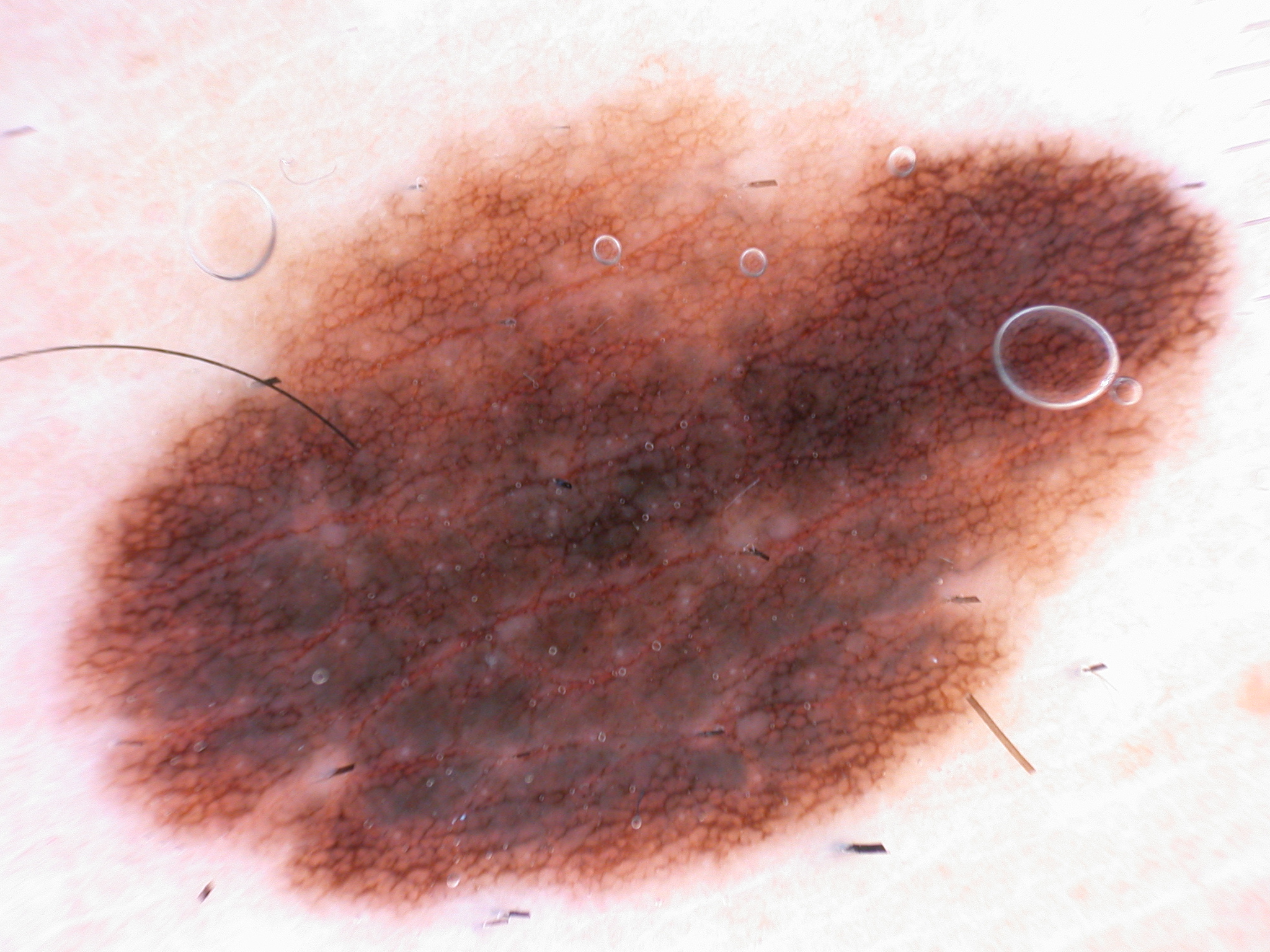Q: What is the imaging modality?
A: dermoscopic image
Q: Which dermoscopic features were noted?
A: pigment network
Q: Where is the lesion in the image?
A: 56, 49, 1233, 924
Q: What did the assessment conclude?
A: a melanocytic nevus, a benign lesion